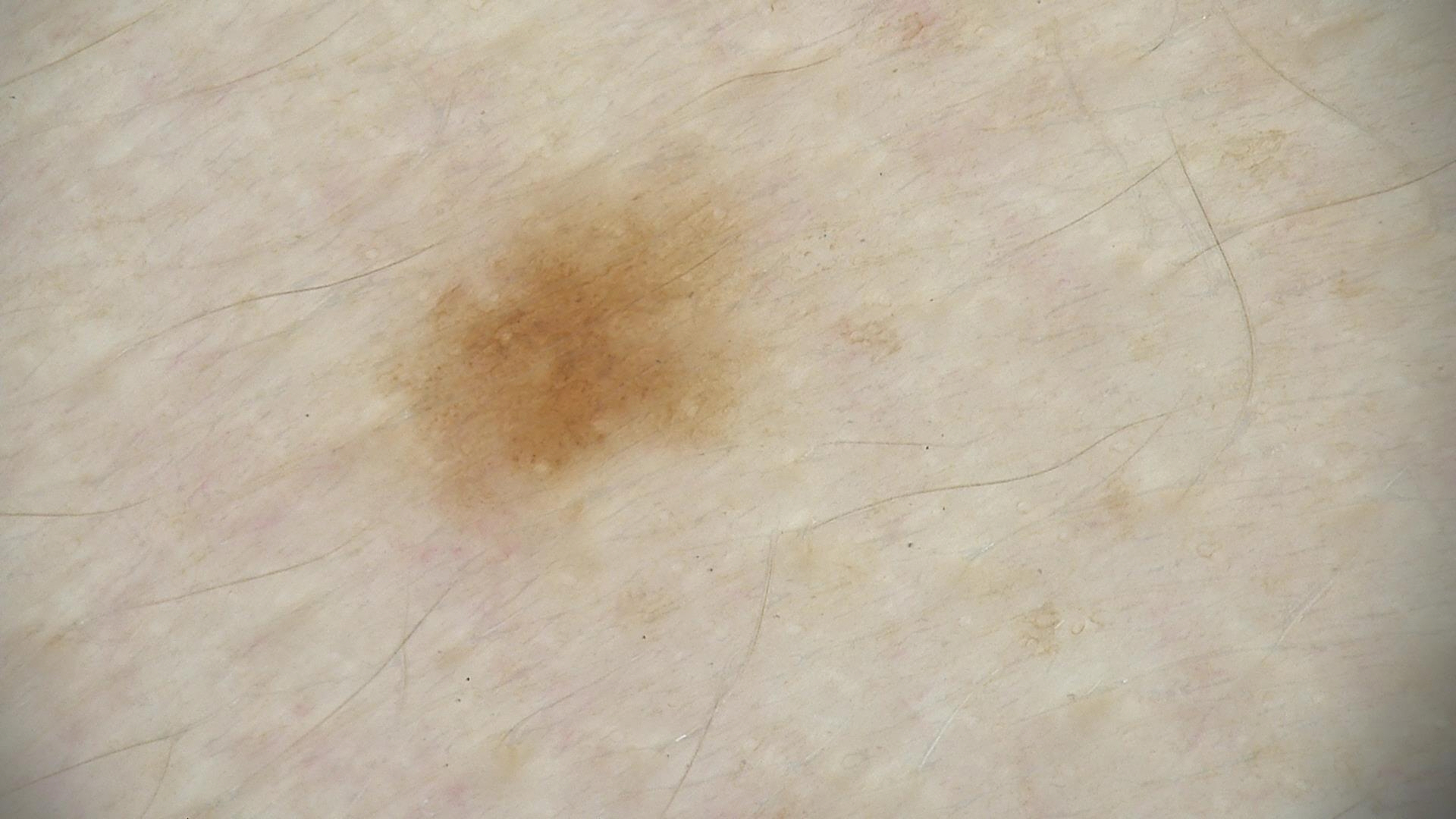A dermoscopic image of a skin lesion. Diagnosed as a dysplastic junctional nevus.